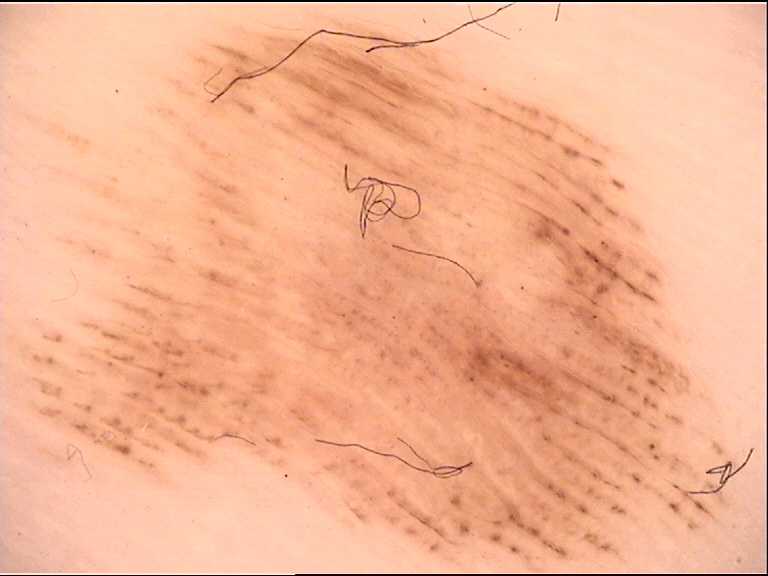| key | value |
|---|---|
| class | acral junctional nevus (expert consensus) |